The chart notes prior skin cancer (patient or family) and no pesticide exposure; a clinical photograph of a skin lesion.
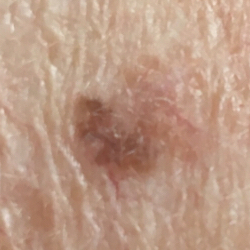Located on the neck.
The lesion measures approximately 6 × 5 mm.
Per patient report, the lesion is not elevated.
Histopathological examination showed a malignant lesion — a squamous cell carcinoma.